A male subject age 79. The patient describes having few moles overall. A macroscopic clinical photograph of a skin lesion. Acquired for a research image collection, with no referral diagnosis. The patient says their skin tans without first burning — 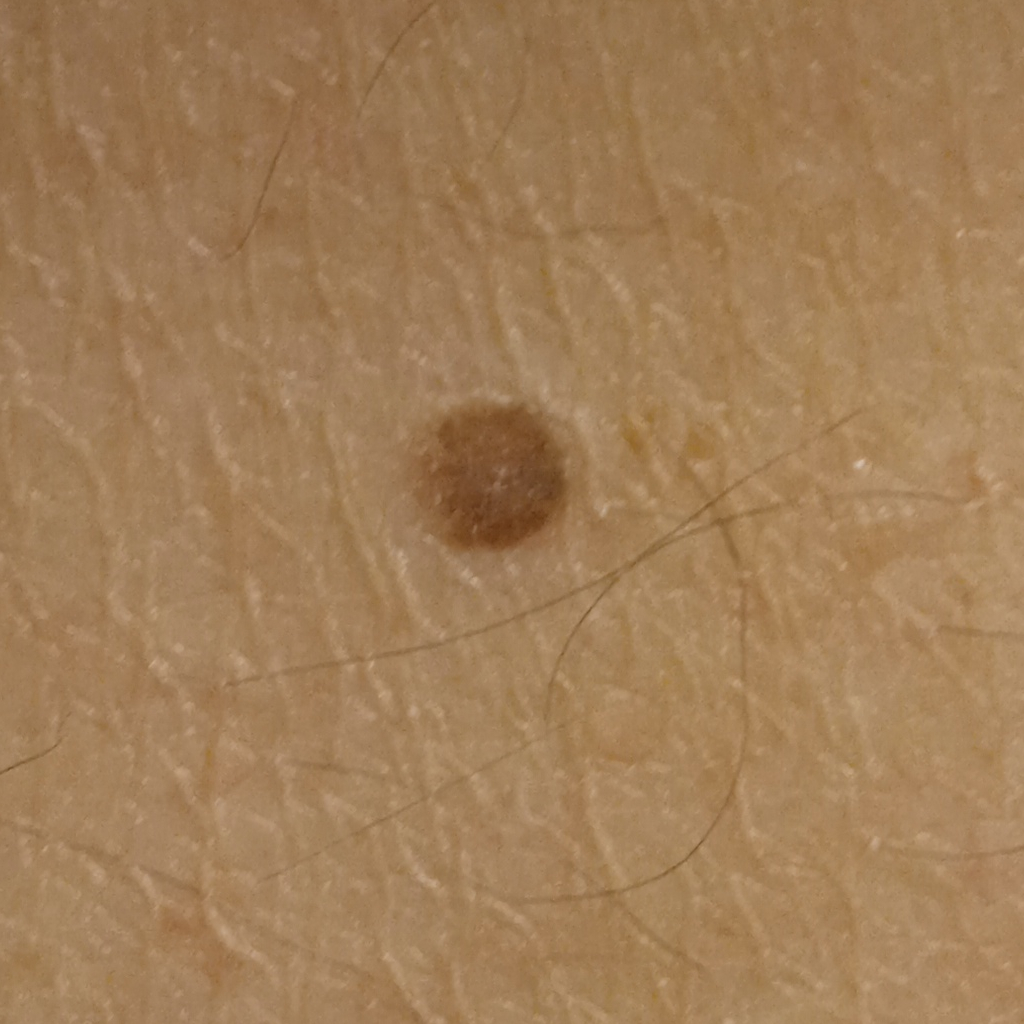lesion_size:
  diameter_mm: 5.8
diagnosis:
  name: melanocytic nevus
  malignancy: benign